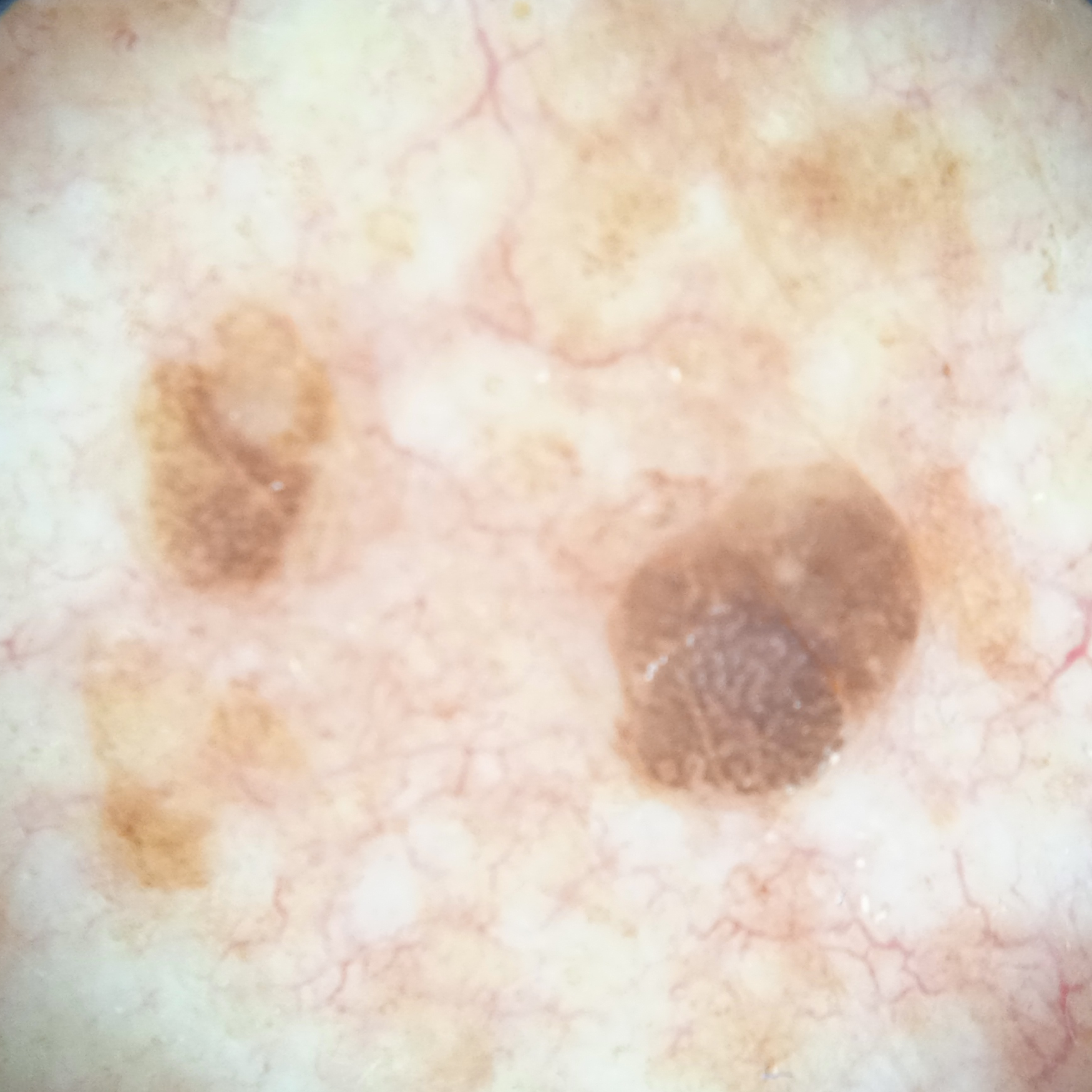{"image": "dermoscopic image", "referral": "research study (no referral diagnosis)", "lesion_size": {"diameter_mm": 4.6}, "diagnosis": {"name": "seborrheic keratosis", "malignancy": "benign"}}